A dermoscopic image of a skin lesion: 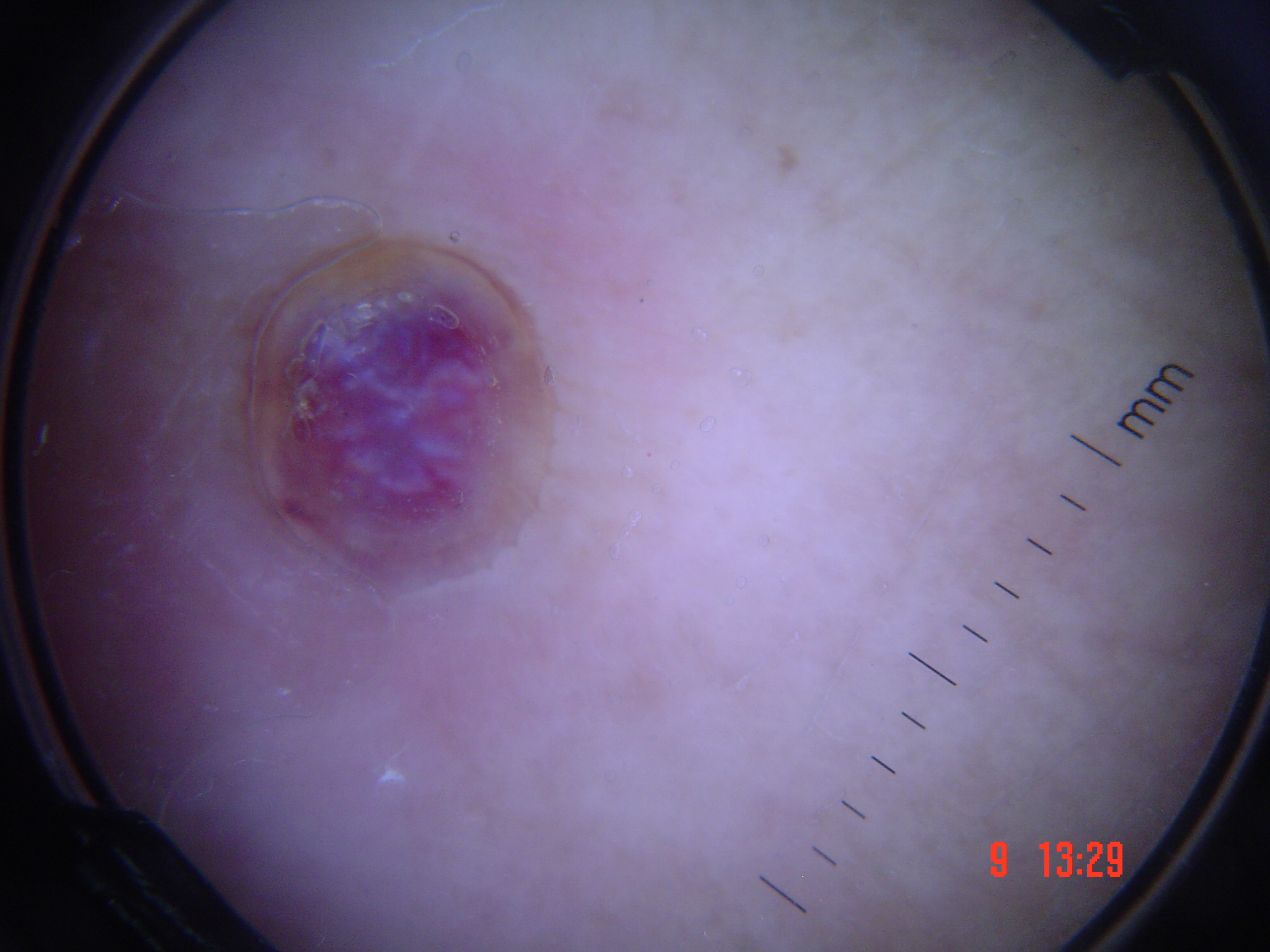The morphology is that of a vascular lesion. Histopathologically confirmed as a skin cancer — a Kaposi sarcoma.